A dermoscopic photograph of a skin lesion: 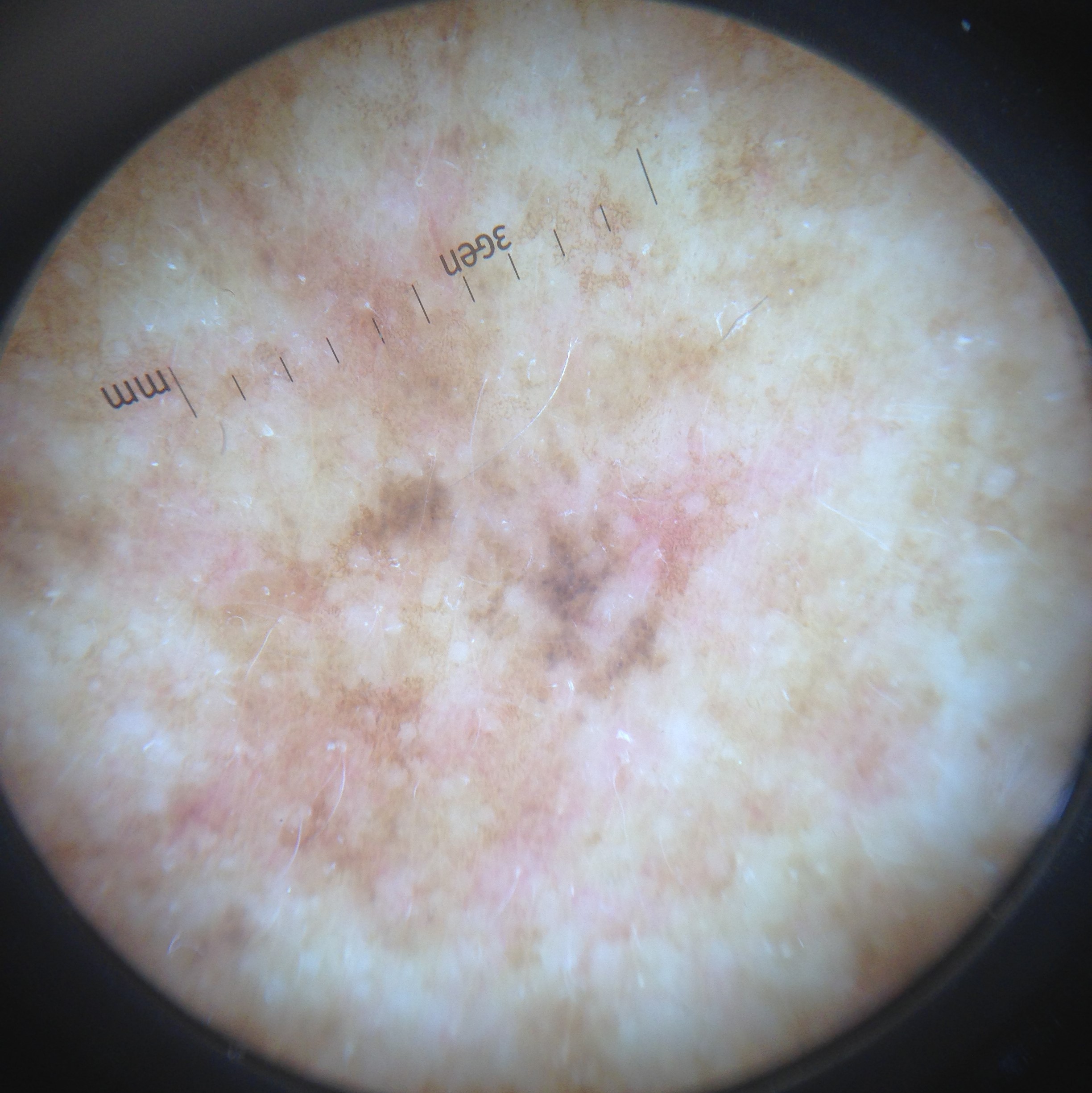The morphology is that of a keratinocytic lesion.
Diagnosed as a lesion with uncertain malignant potential — an actinic keratosis.